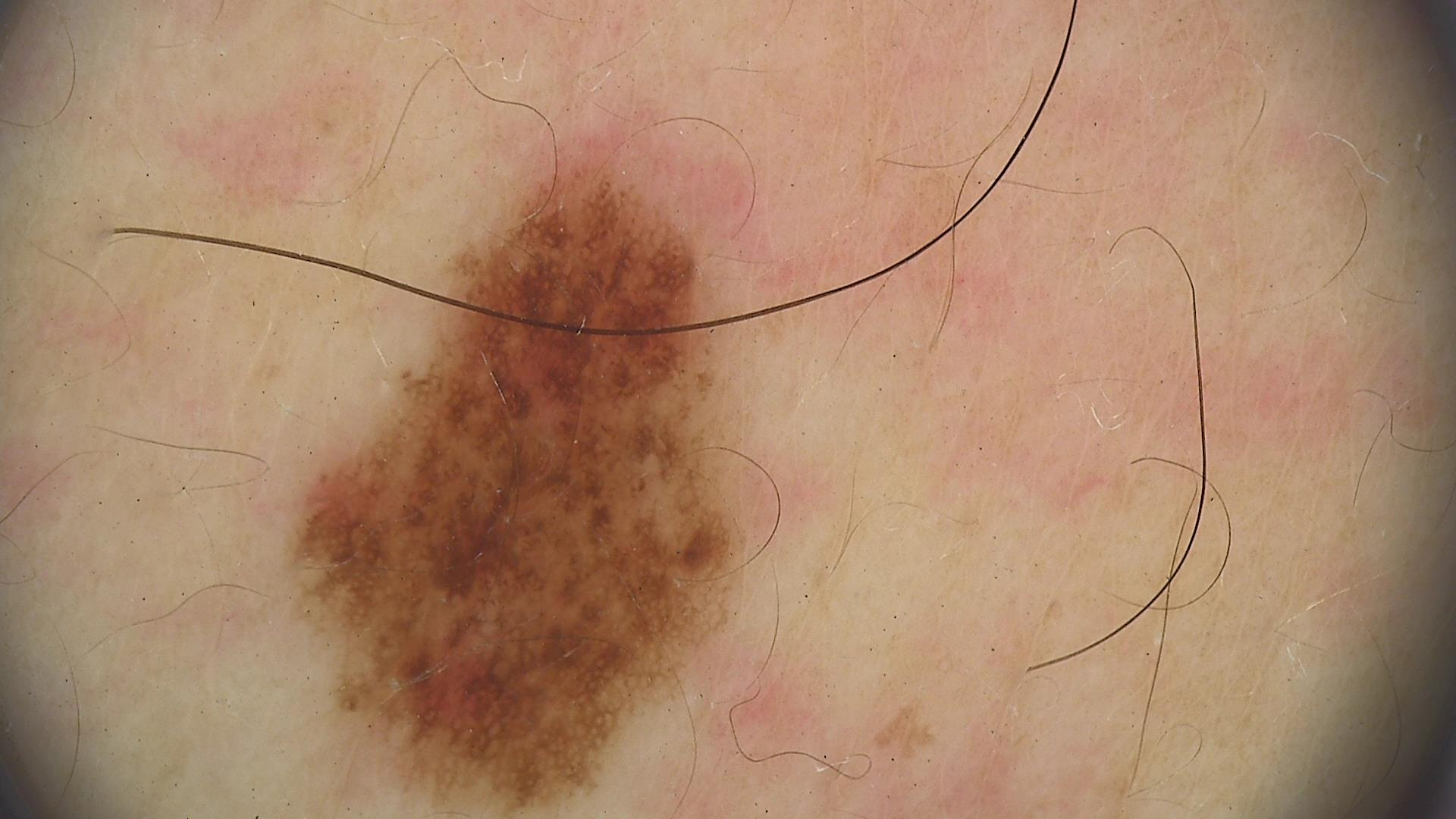Conclusion:
The diagnostic label was a dysplastic junctional nevus.